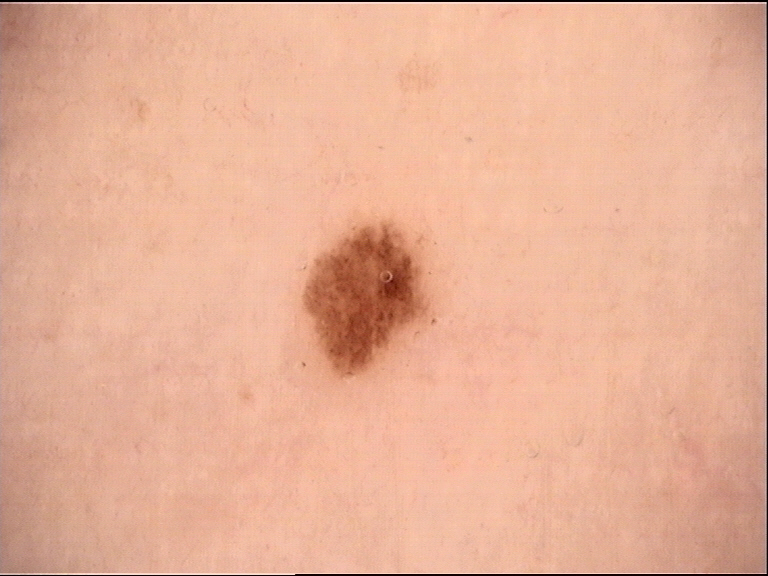Q: What is the imaging modality?
A: dermoscopy
Q: What was the diagnostic impression?
A: dysplastic junctional nevus (expert consensus)